The patient is 30–39, female. Symptoms reported: burning, enlargement, itching and bothersome appearance. The leg, head or neck and back of the hand are involved. This is a close-up image. Reported duration is one to four weeks. The patient considered this a rash — 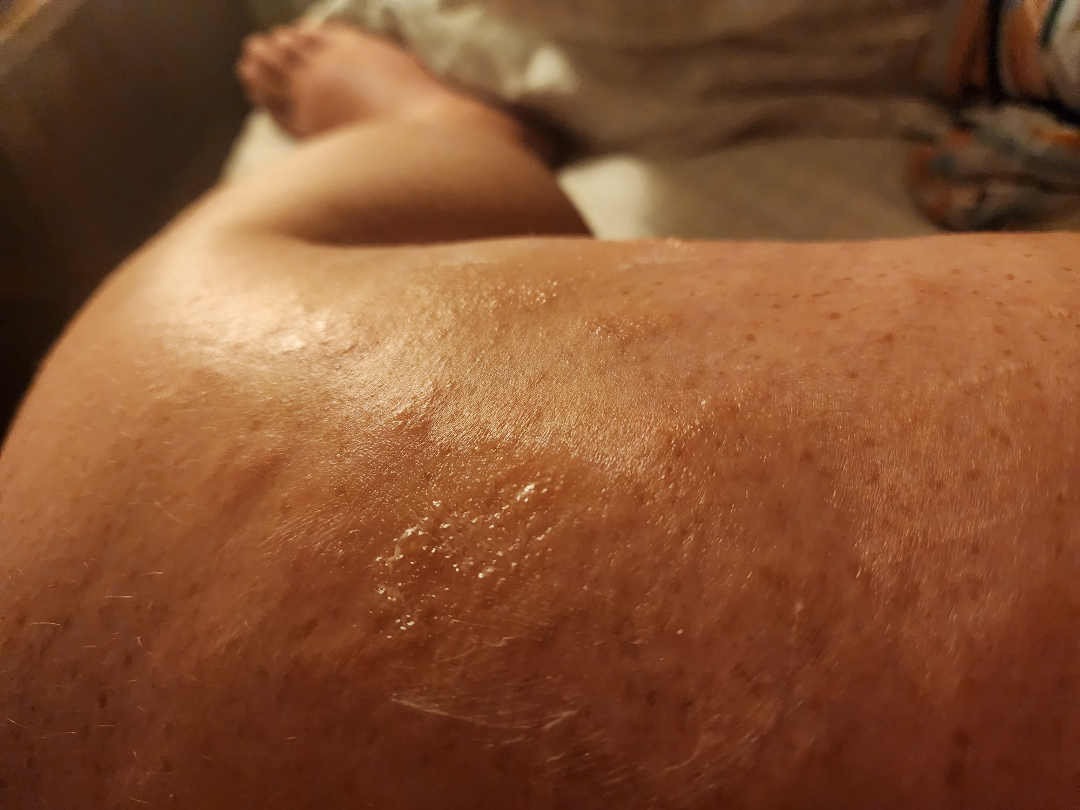On photographic review: the leading consideration is Urticaria; also consider Herpes Zoster; possibly Allergic Contact Dermatitis; less likely is Insect Bite.